The patient considered this a rash · present for one to four weeks · associated systemic symptoms include fatigue and joint pain · the subject is 50–59, female · an image taken at an angle · the lesion is associated with burning and itching: 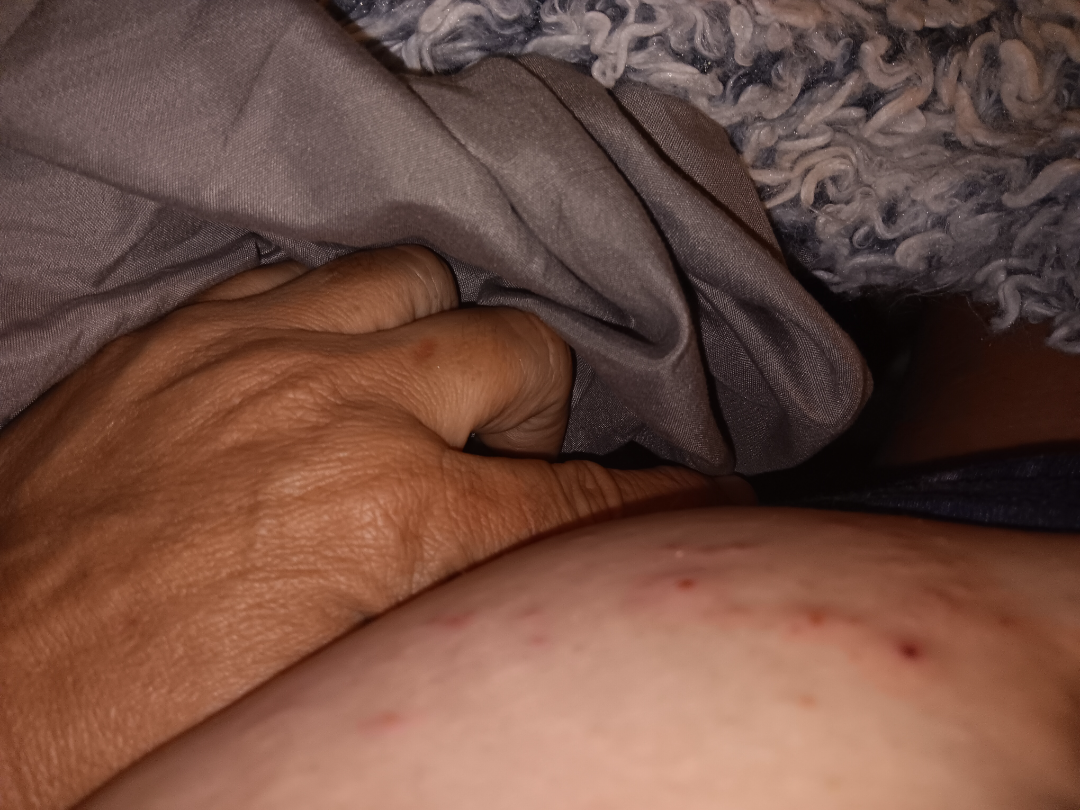| key | value |
|---|---|
| assessment | indeterminate |